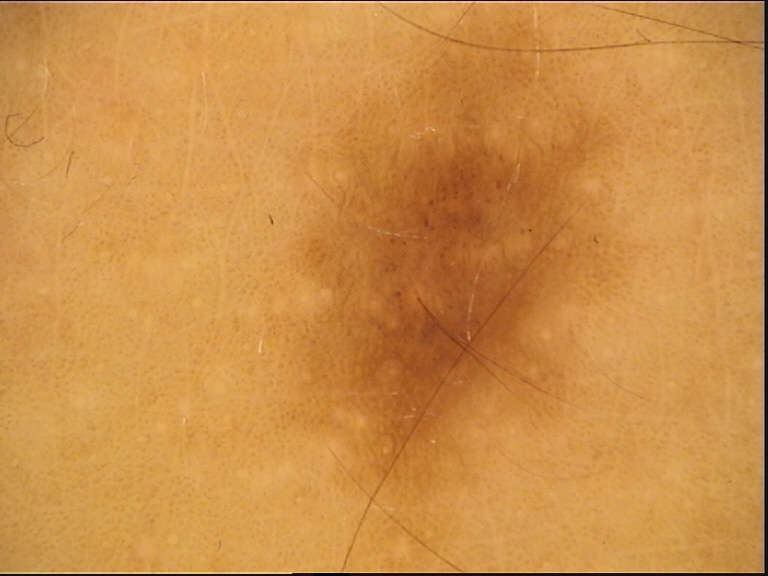A dermoscopic photograph of a skin lesion. Labeled as a benign lesion — a dysplastic junctional nevus.